This is a dermoscopic photograph of a skin lesion; a female subject about 30 years old.
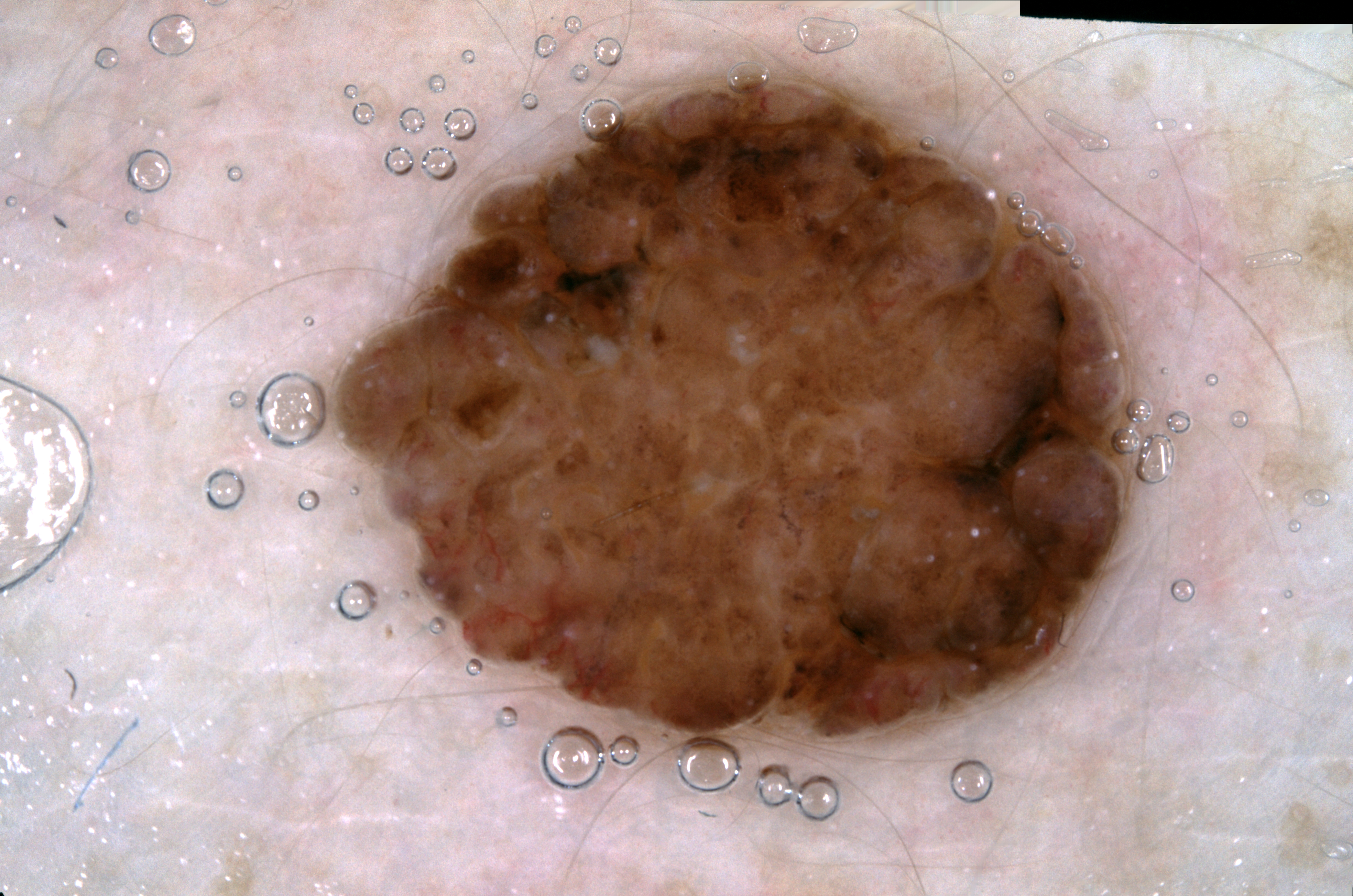In (x1, y1, x2, y2) order, the lesion spans 333 72 1138 769. Dermoscopy demonstrates no negative network, streaks, pigment network, or milia-like cysts. The lesion covers approximately 32% of the dermoscopic field. Expert review diagnosed this as a melanocytic nevus.